Dermoscopy of a skin lesion.
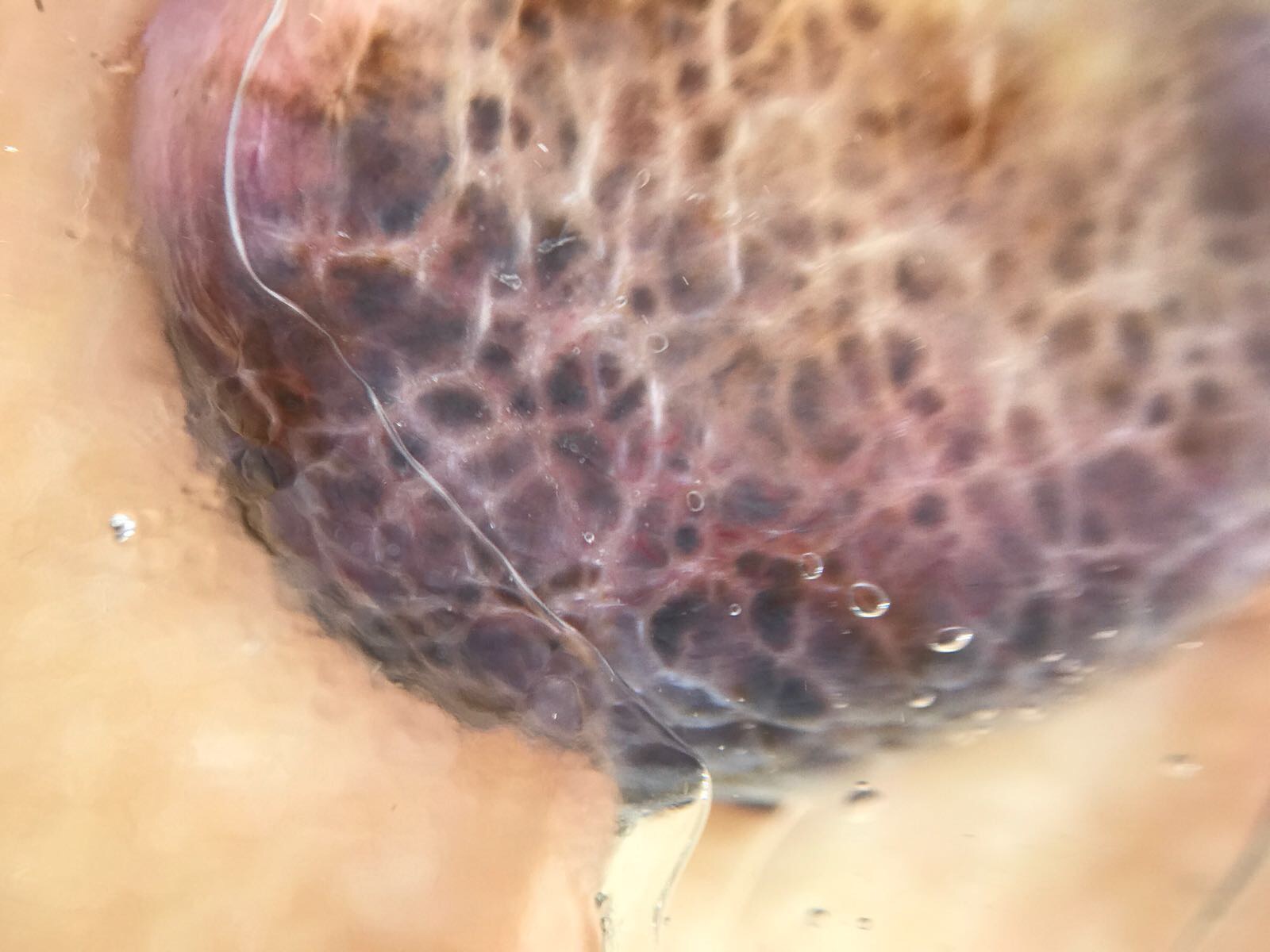Pathology: The biopsy diagnosis was a melanoma.